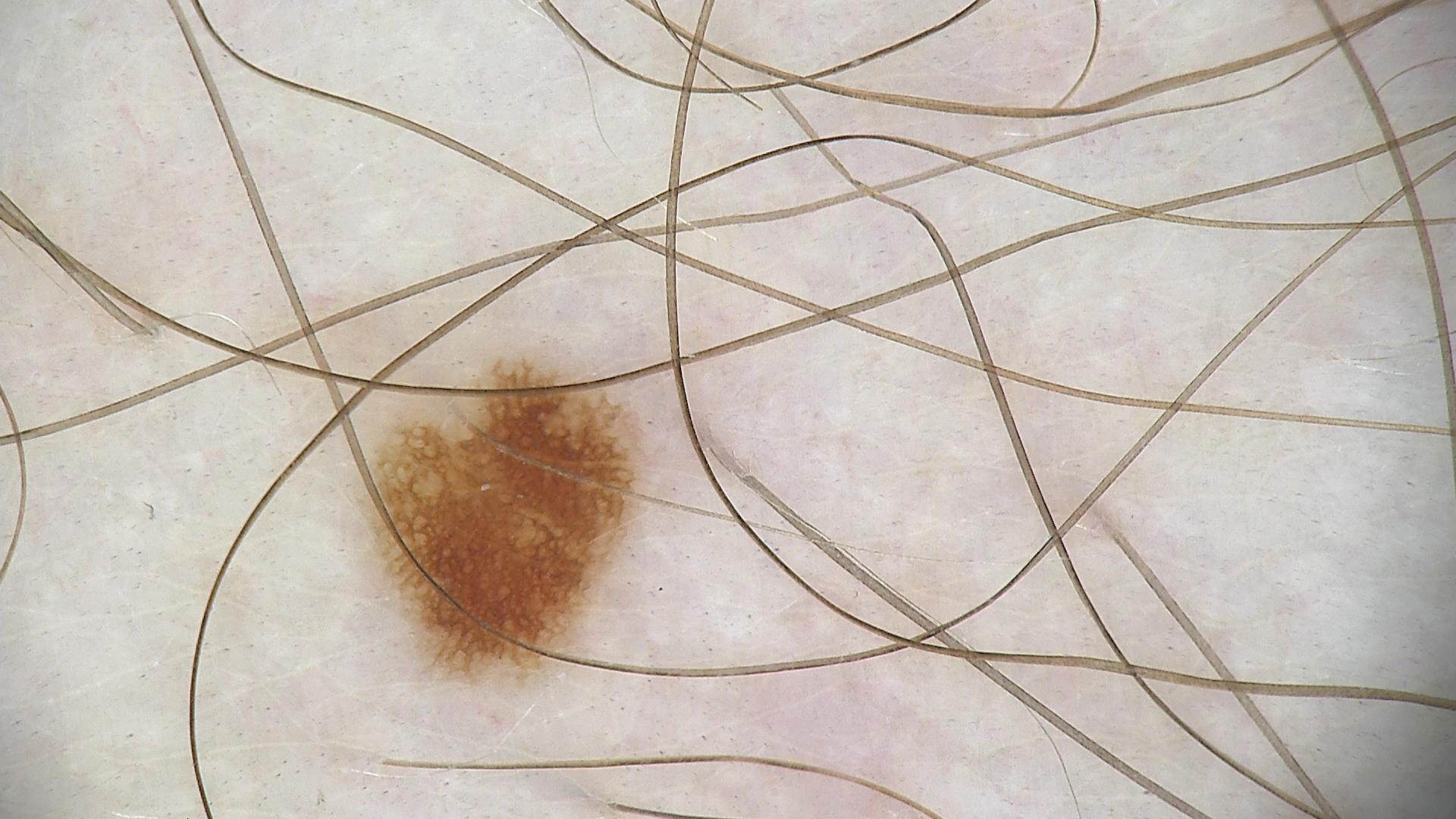Conclusion: Labeled as a benign lesion — a dysplastic junctional nevus.